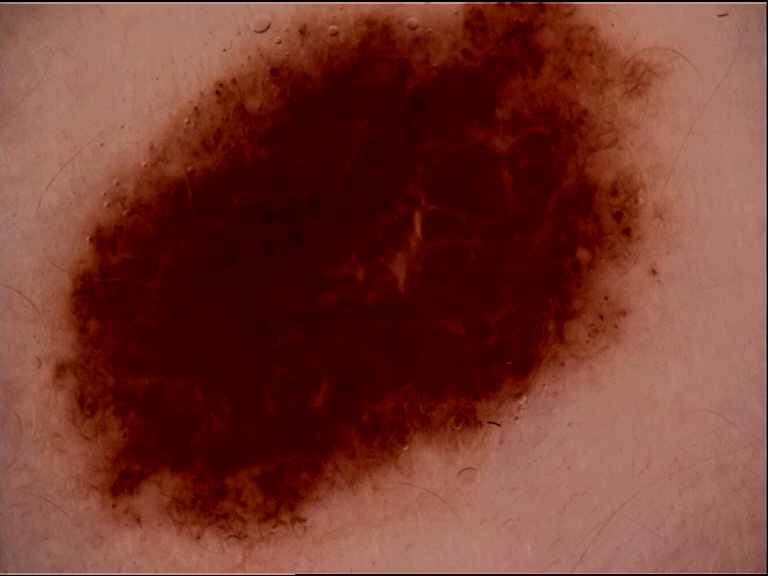A dermoscopic image of a skin lesion.
The diagnosis was a benign lesion — a dysplastic compound nevus.